The affected area is the top or side of the foot · the photograph is a close-up of the affected area:
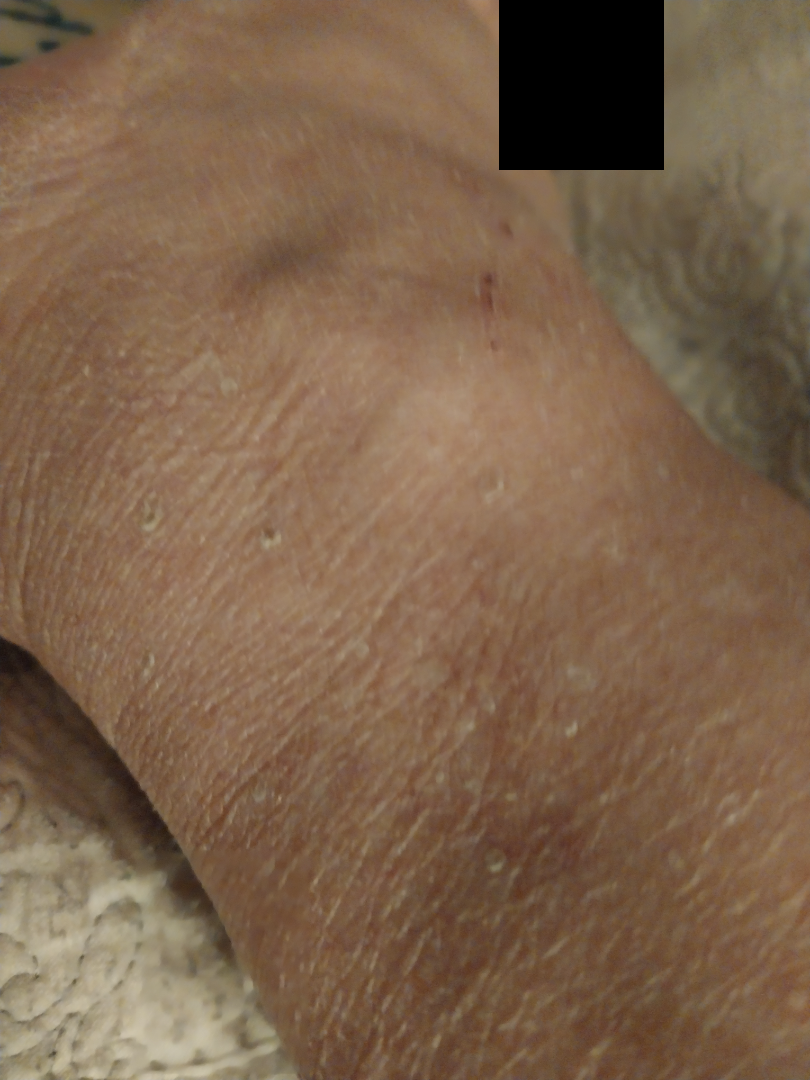reported symptoms = itching, lesion texture = raised or bumpy, patient's own categorization = a rash, onset = more than one year, differential = most consistent with Eczema.